A dermatoscopic image of a skin lesion.
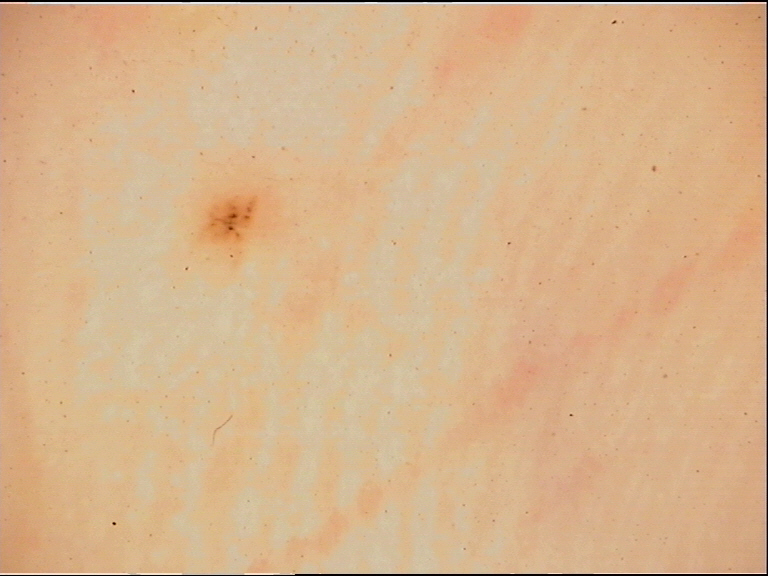assessment: acral junctional nevus (expert consensus)